The head or neck is involved. This is a close-up image:
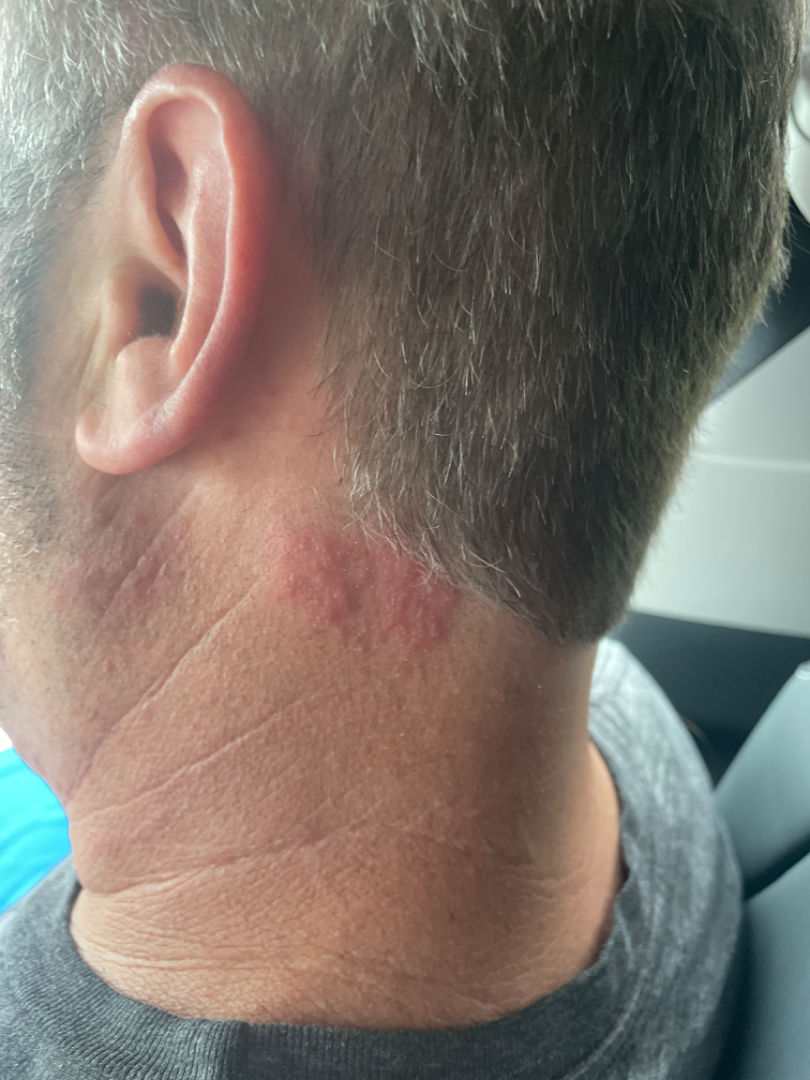On remote dermatologist review, the differential is split between Tinea and Cutaneous T Cell Lymphoma.